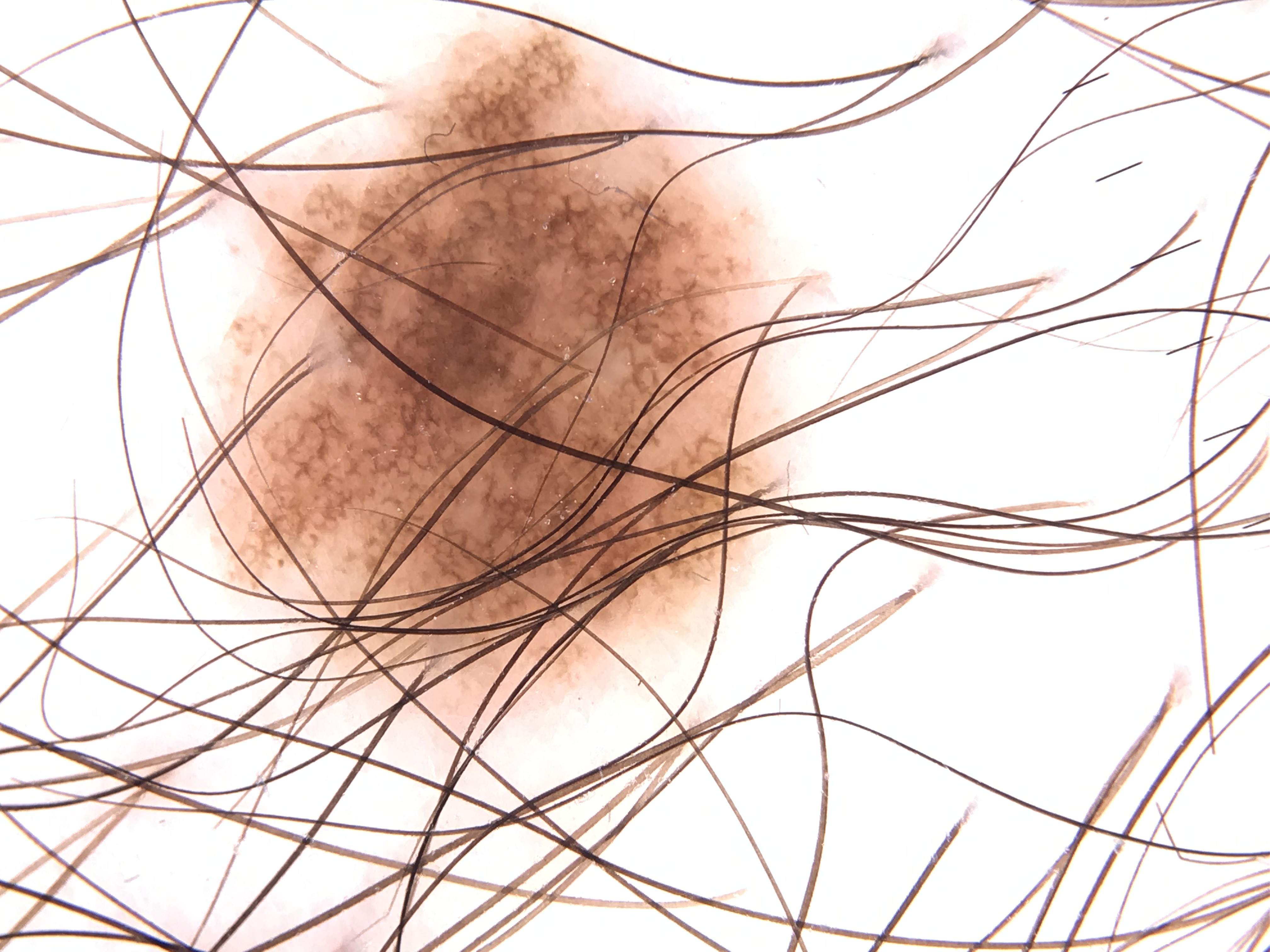A dermoscopic photograph of a skin lesion.
The diagnosis was a dysplastic junctional nevus.